A clinical photo of a skin lesion taken with a smartphone · a female patient aged 75: 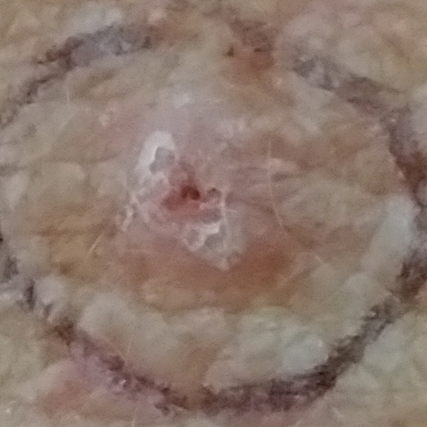anatomic site = the back | patient-reported symptoms = itching / no elevation | diagnosis = actinic keratosis (biopsy-proven).